The affected area is the head or neck; a close-up photograph — 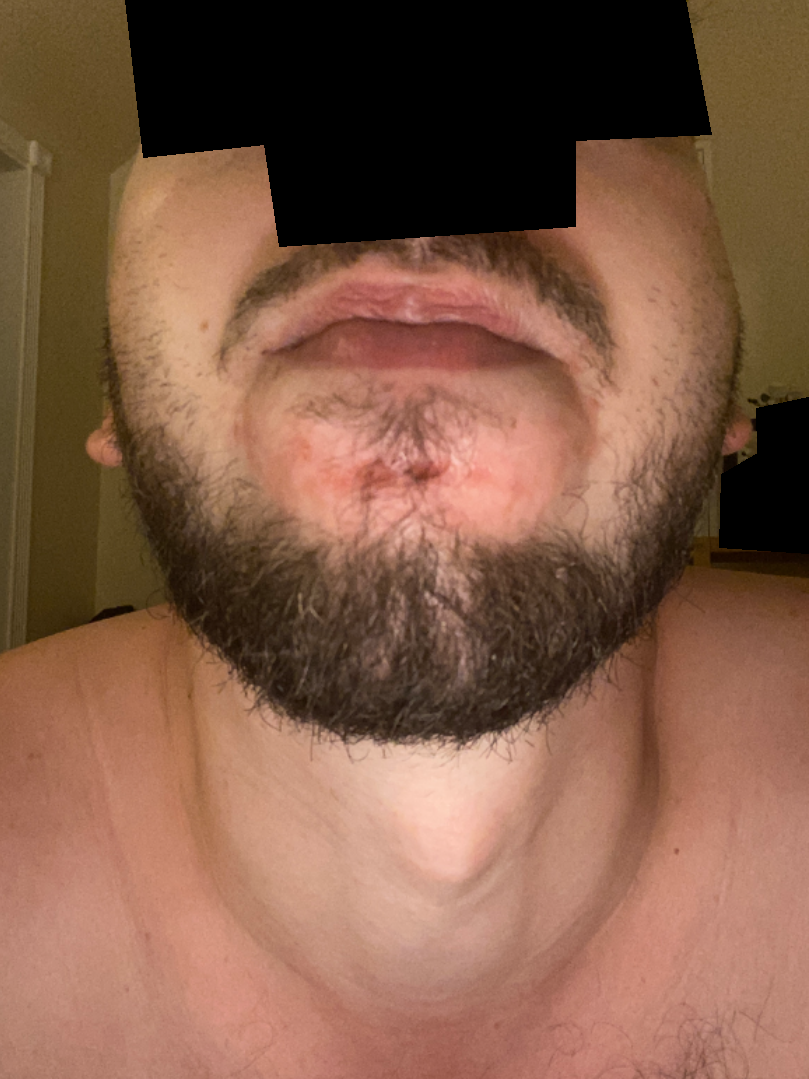On teledermatology review, most likely Seborrheic Dermatitis; also consider Impetigo; with consideration of Psoriasis.